A dermoscopic close-up of a skin lesion:
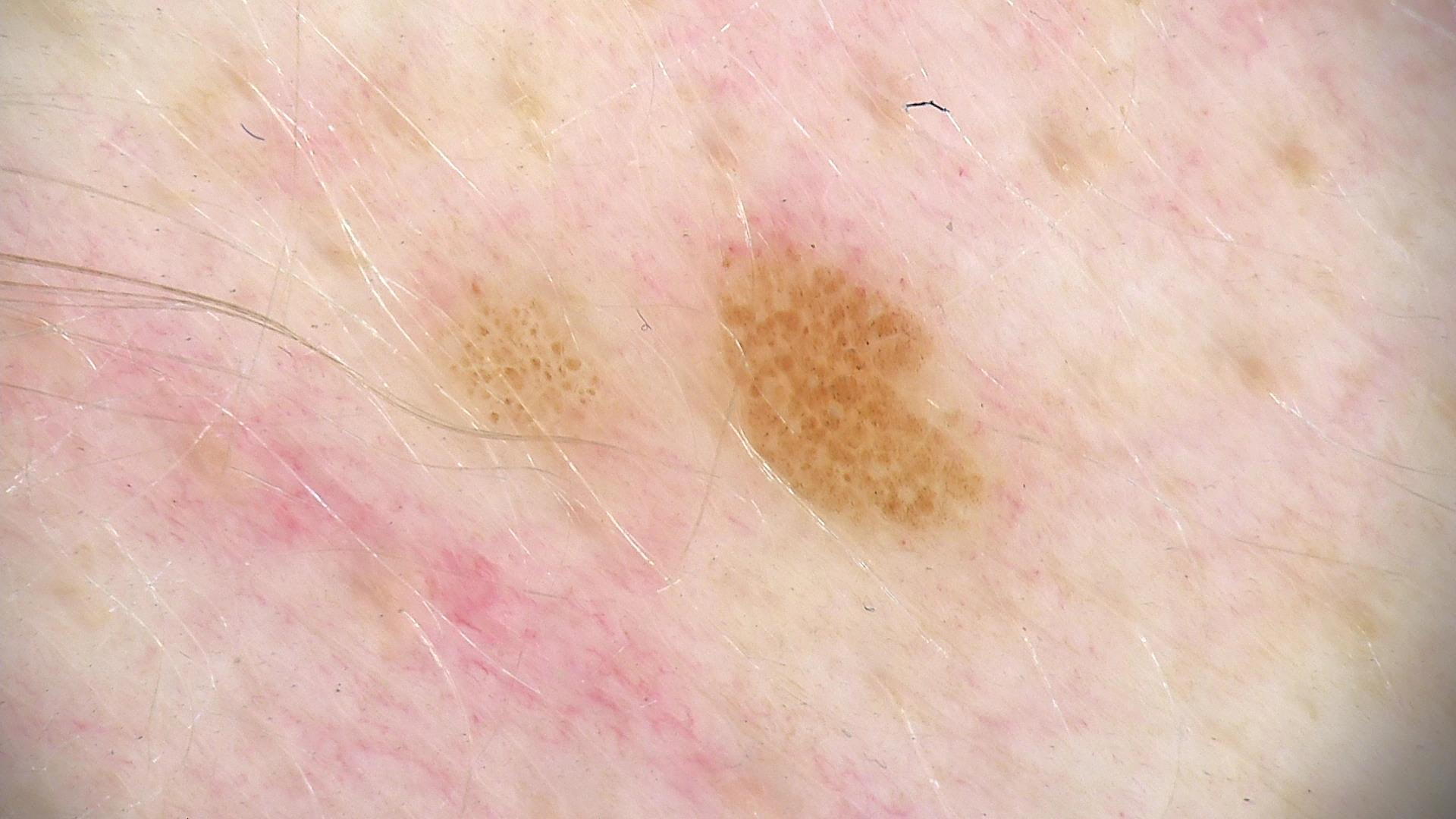Impression:
Consistent with a banal lesion — a junctional nevus.